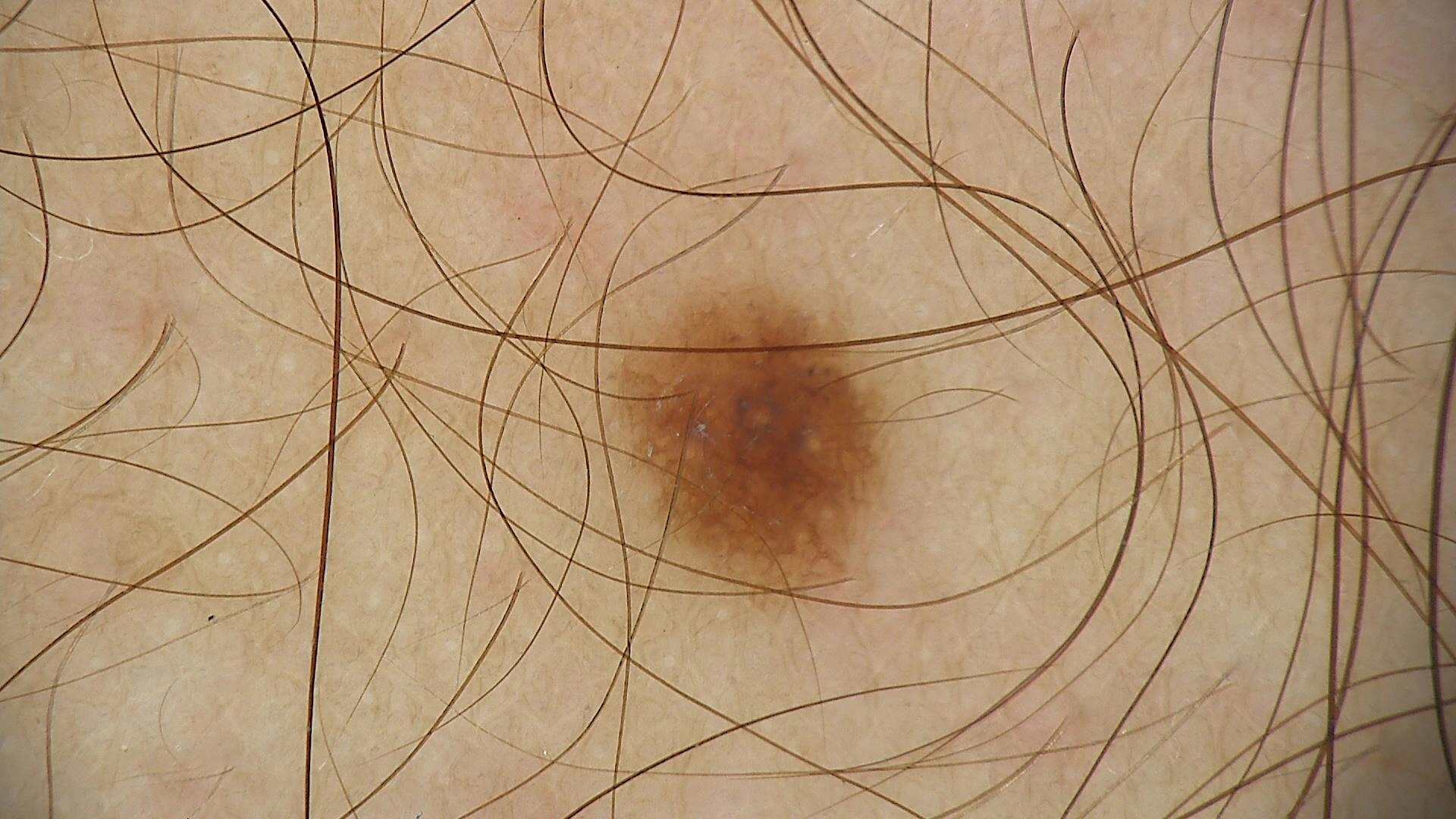Case:
• modality: dermoscopy
• class: dysplastic junctional nevus (expert consensus)